Present for less than one week · the patient considered this a rash · the lesion involves the leg · this image was taken at a distance · the subject is 30–39, male · the contributor notes the lesion is flat.
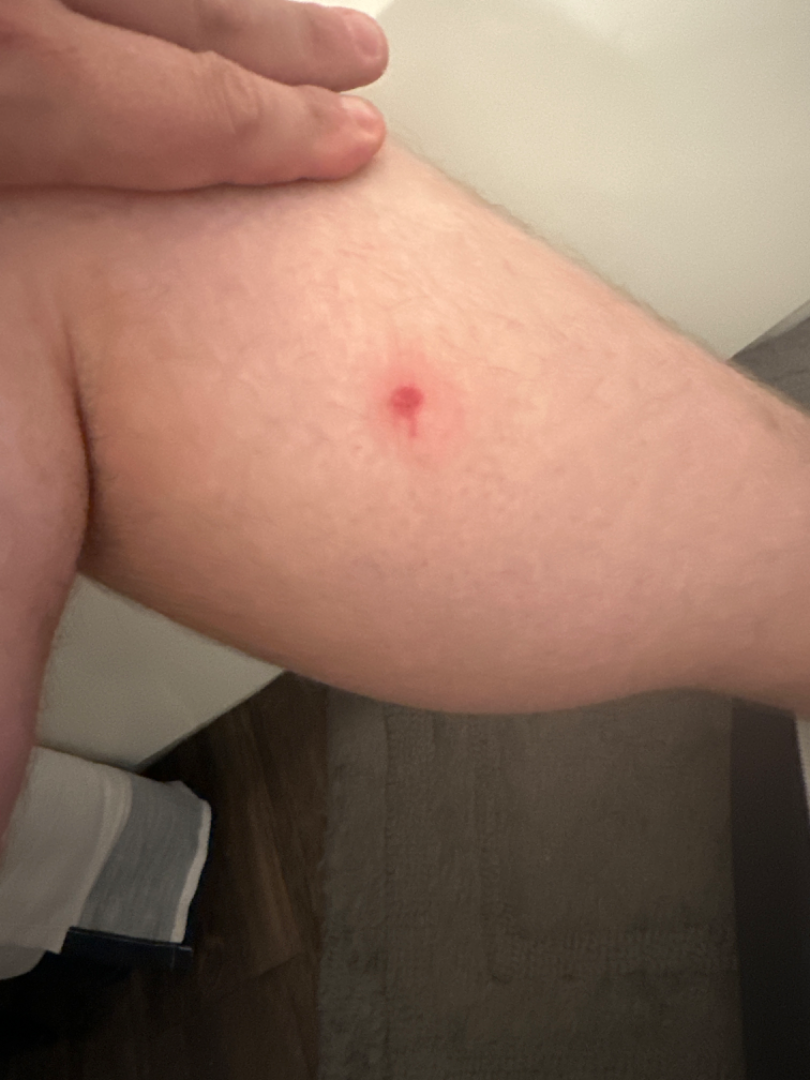Reviewed remotely by one dermatologist: the impression was split between Inflicted skin lesions, Insect Bite and Localized skin infection.